A male patient in their mid-40s; the patient is Fitzpatrick phototype II; a clinical photograph of a skin lesion; the chart records pesticide exposure, prior skin cancer (patient or family), no tobacco use, and no alcohol use:
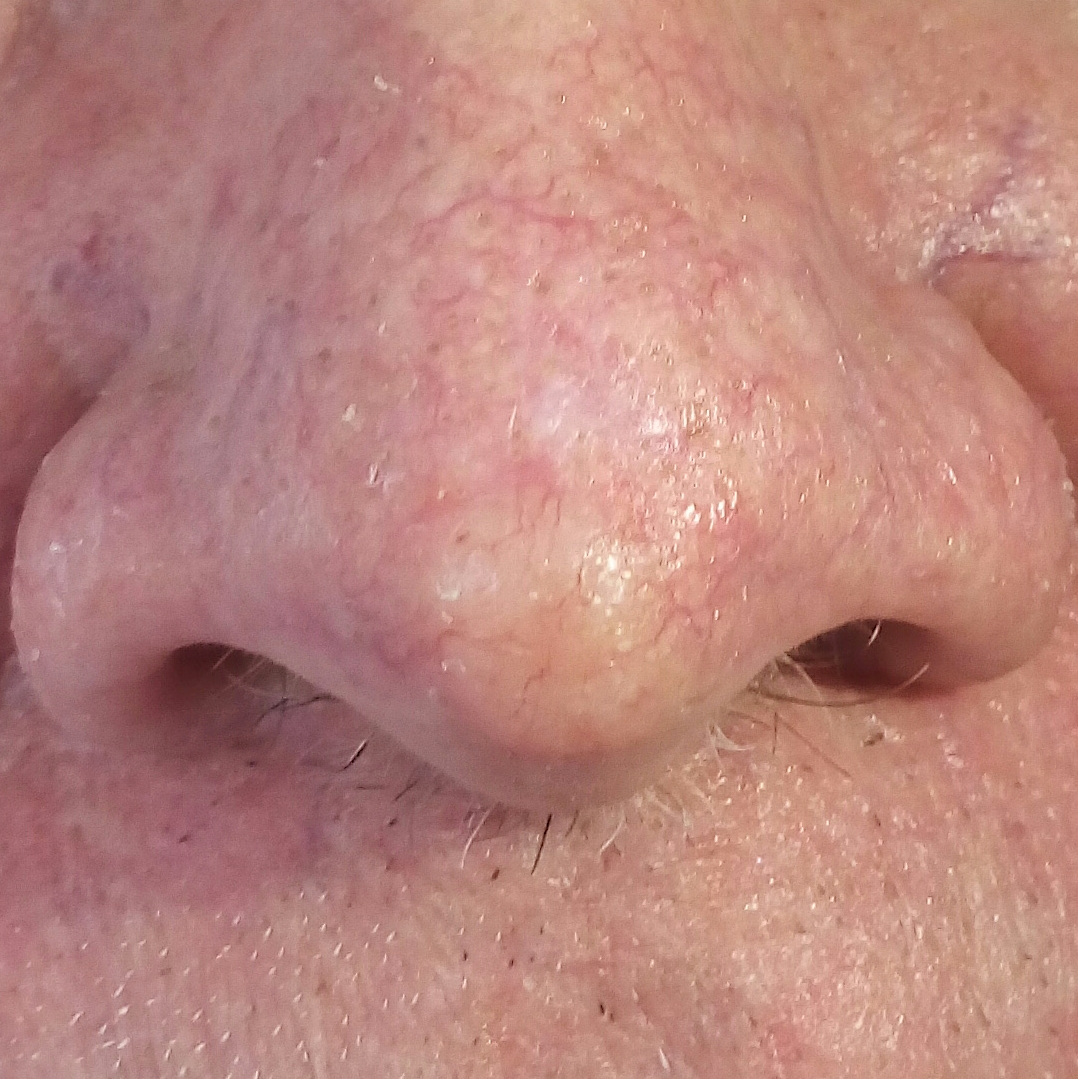{
  "lesion_location": "the nose",
  "lesion_size": {
    "diameter_1_mm": 10.0,
    "diameter_2_mm": 10.0
  },
  "symptoms": {
    "present": [
      "growth",
      "elevation",
      "itching"
    ],
    "absent": [
      "change in appearance"
    ]
  },
  "diagnosis": {
    "name": "basal cell carcinoma",
    "code": "BCC",
    "malignancy": "malignant",
    "confirmation": "histopathology"
  }
}